A female patient age 67. The patient says their skin tans without first burning. Dermoscopy of a skin lesion. Imaged for a research study, with no referral diagnosis recorded. Few moles overall by the patient's own estimate.
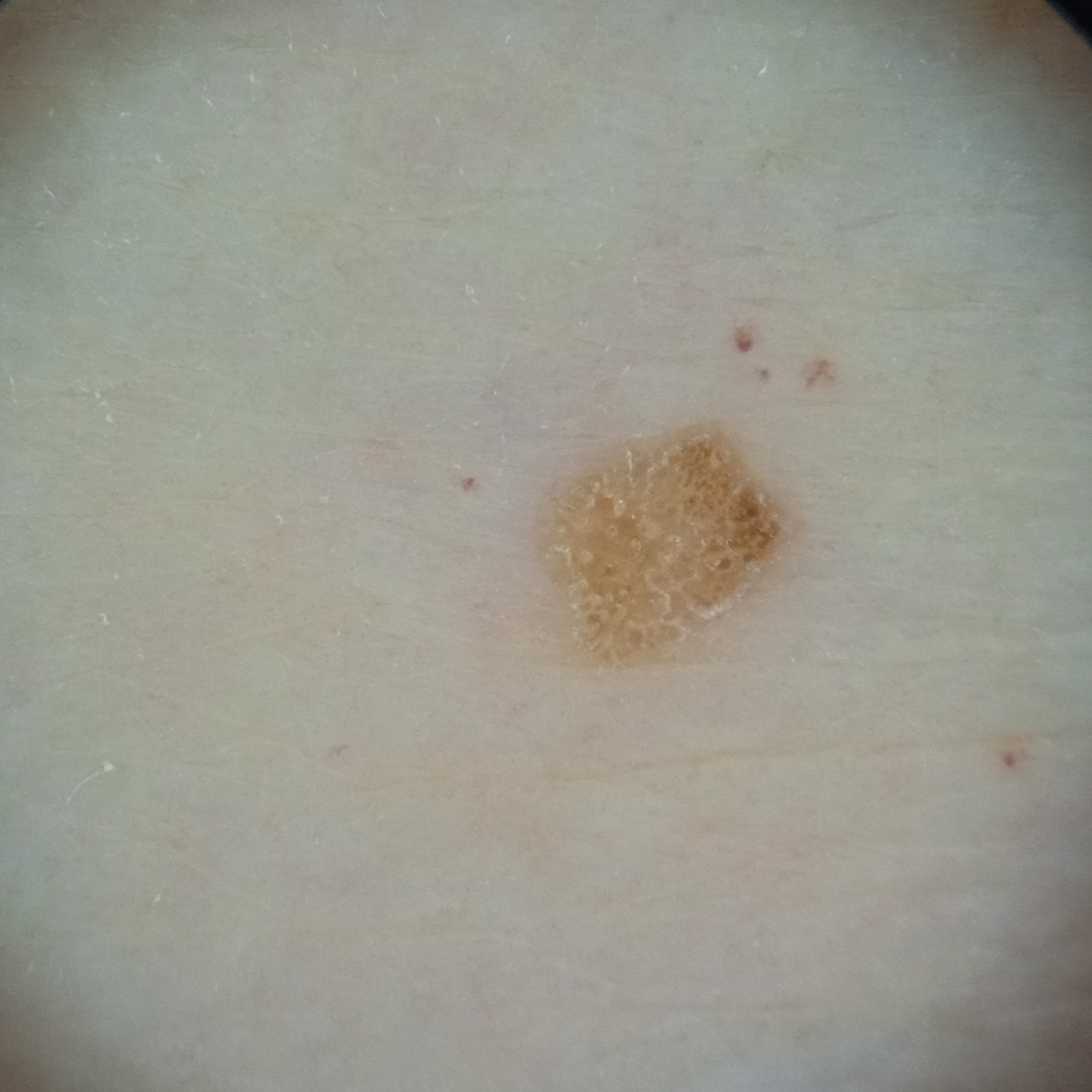Located on an arm. The lesion measures approximately 3.1 mm. The dermatologists' assessment was a seborrheic keratosis.